A dermoscopic image of a skin lesion.
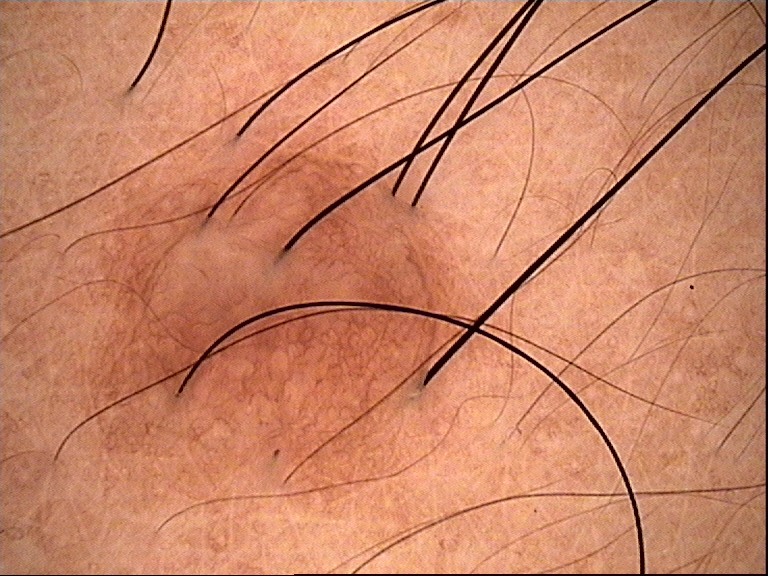The diagnosis was a banal lesion — a dermal nevus.